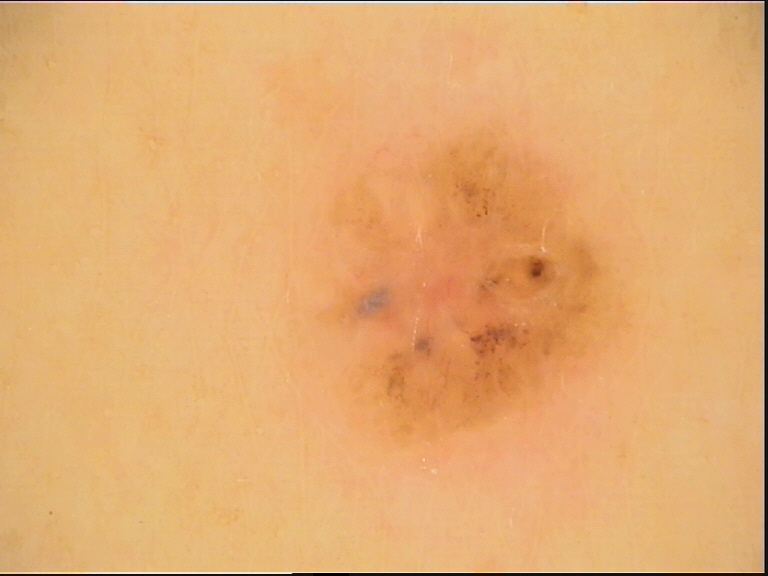imaging = dermatoscopy, lesion type = keratinocytic, pathology = basal cell carcinoma (biopsy-proven).